Collected as part of a research study, without a referral diagnosis.
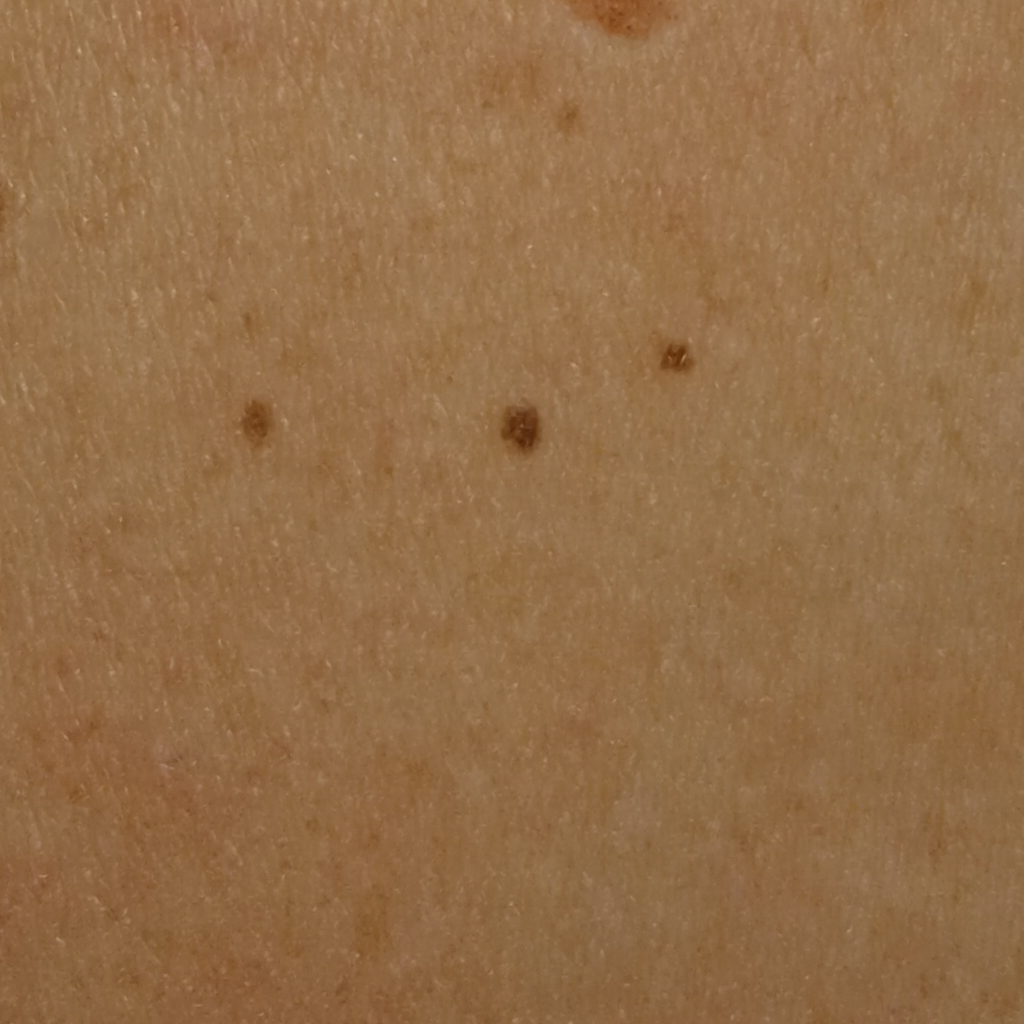size: 2.5 mm | diagnostic label: melanocytic nevus (dermatologist consensus).